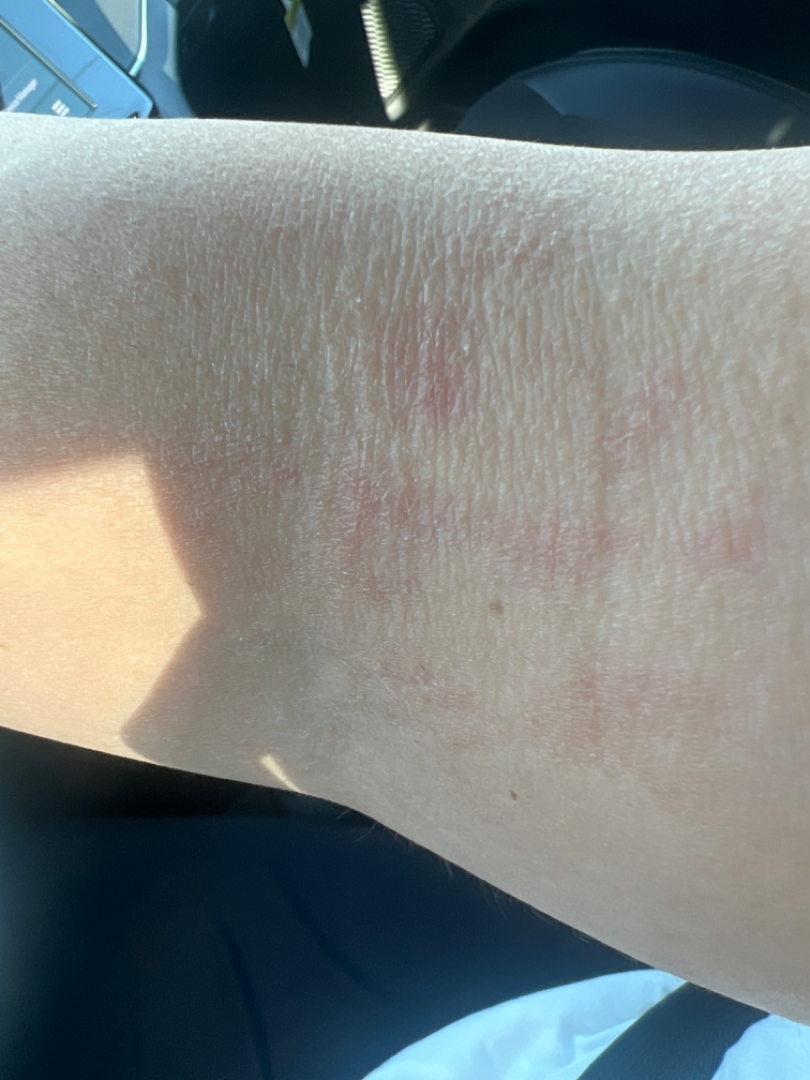History: Female patient, age 30–39. The affected area is the arm. A close-up photograph. The lesion is described as rough or flaky. The patient considered this skin that appeared healthy to them. Present for about one day. Reported lesion symptoms include bothersome appearance. FST II; lay graders estimated 2 on the MST. Impression: In keeping with Eczema.